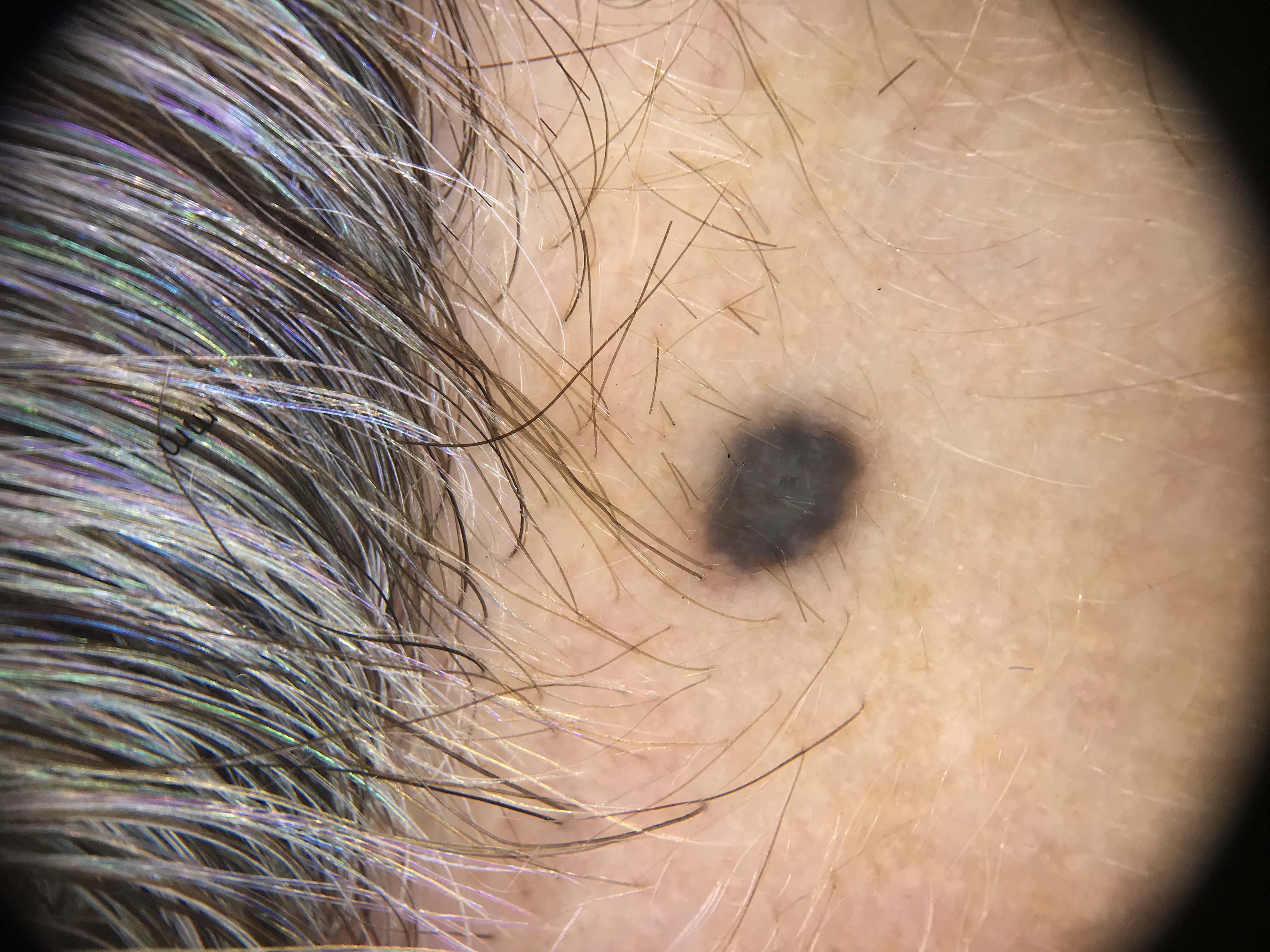A dermoscopic close-up of a skin lesion. Classified as a banal lesion — a blue nevus.